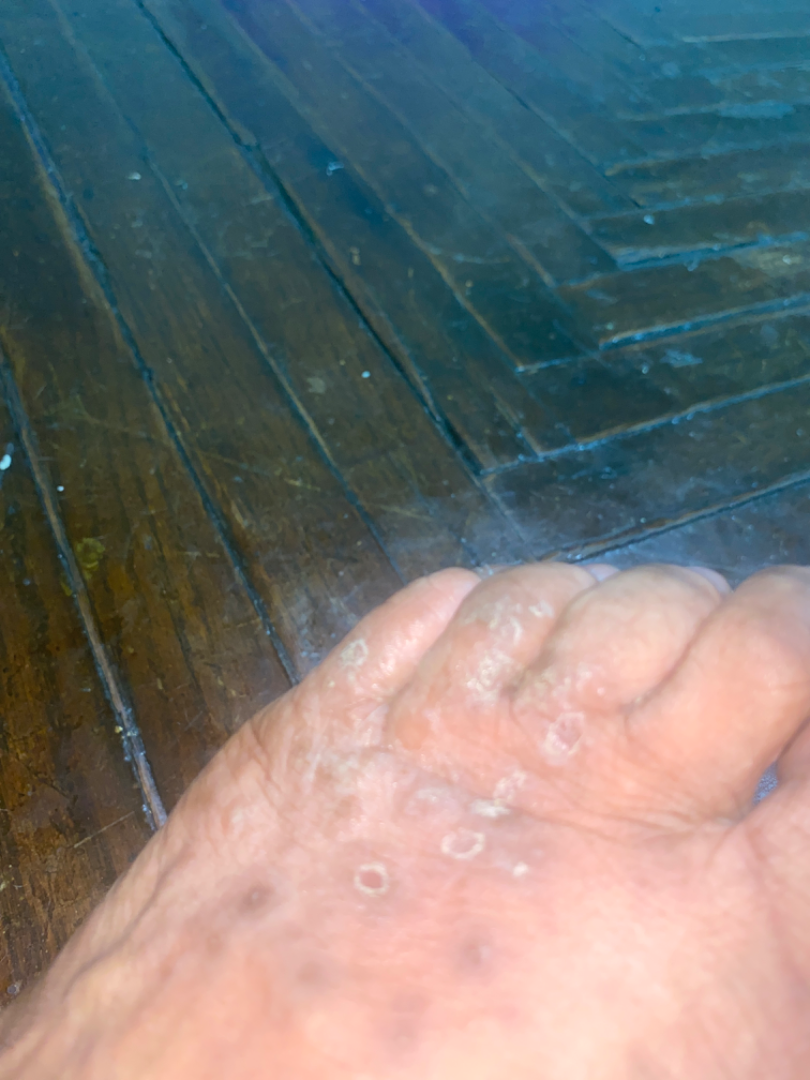framing: at an angle
location: top or side of the foot
diagnostic considerations: Drug Rash (considered); Psoriasiform dermatitis (considered)